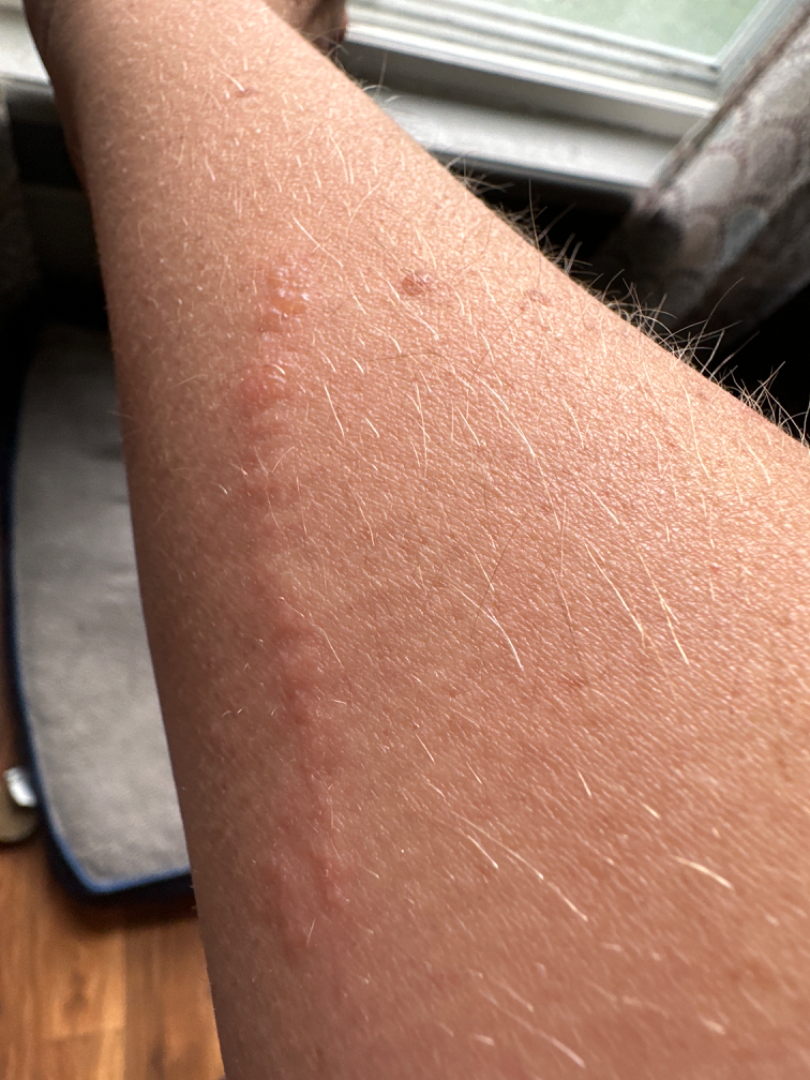– assessment — unable to determine
– reported symptoms — itching
– contributor — female, age 30–39
– patient's own categorization — a rash
– duration — one to four weeks
– lesion texture — raised or bumpy
– other reported symptoms — none reported
– anatomic site — arm
– framing — at an angle